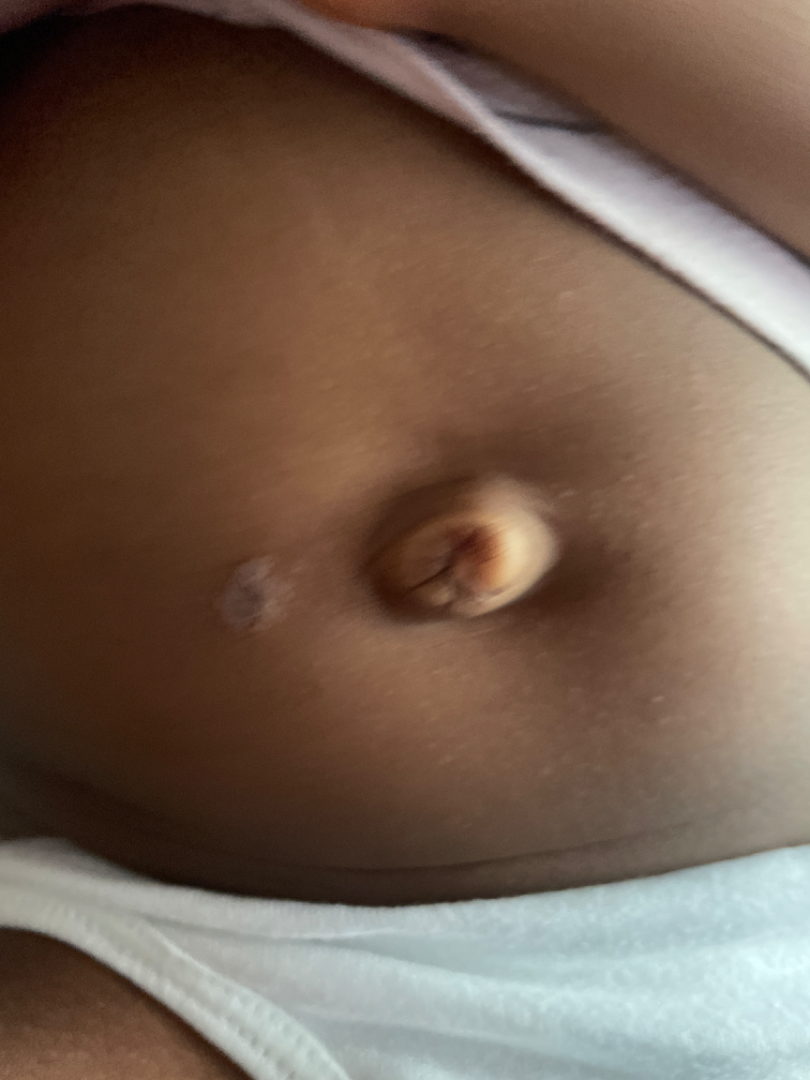Q: What was the assessment?
A: ungradable on photographic review
Q: How was the photo taken?
A: close-up